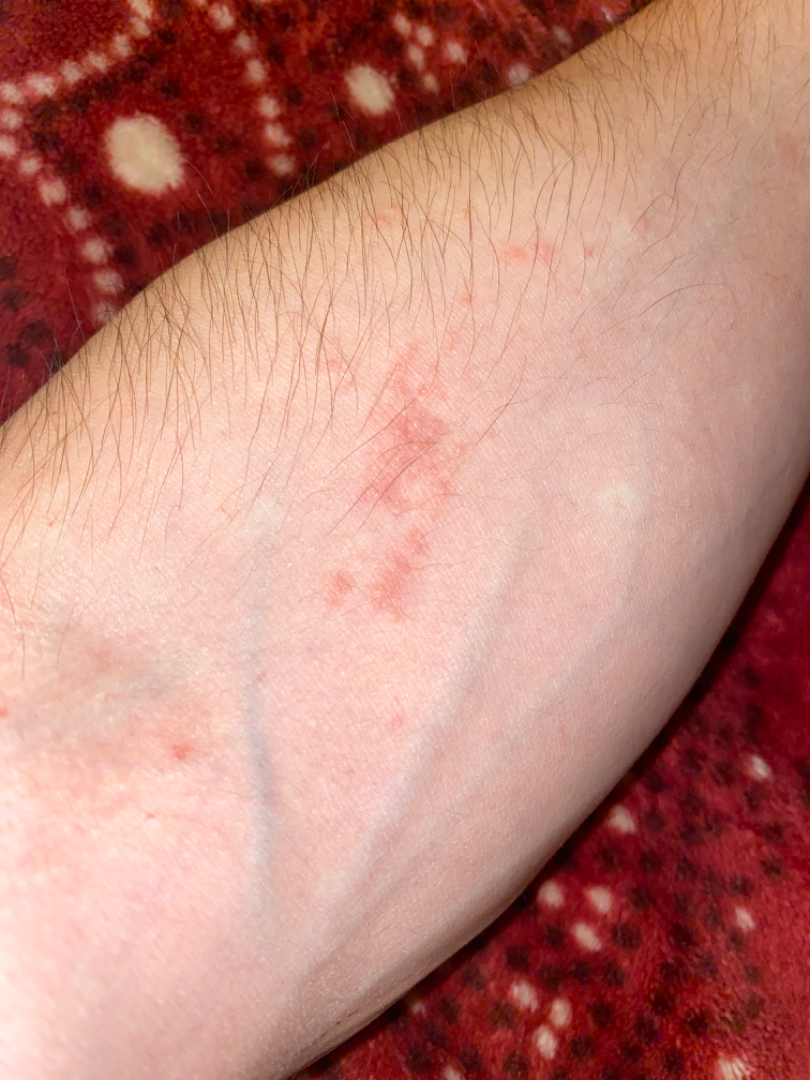Assessment:
Most likely Allergic Contact Dermatitis; also consider Eczema.